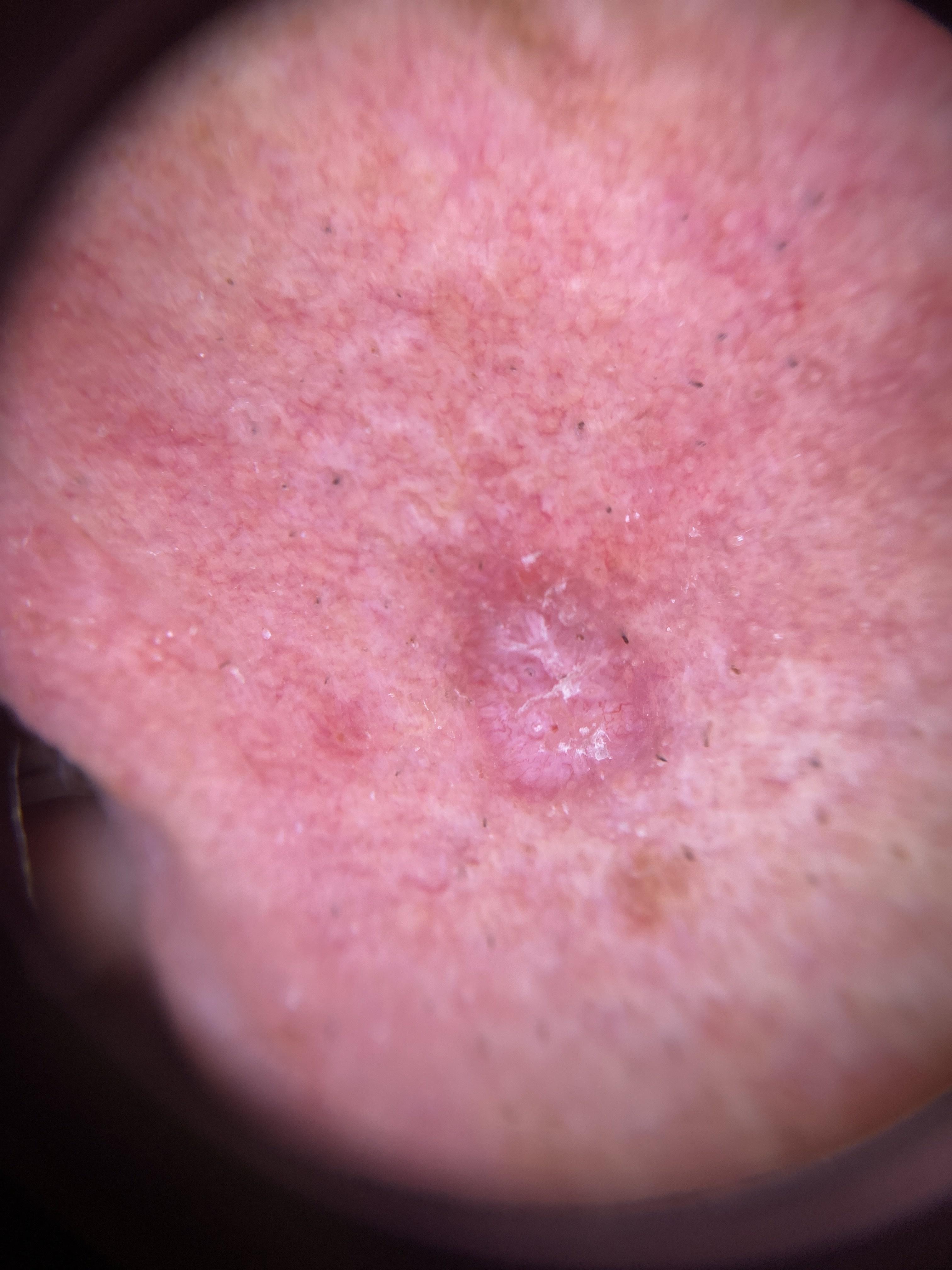The chart records a prior melanoma.
A dermoscopic close-up of a skin lesion.
A male patient approximately 80 years of age.
The lesion is on the head or neck.
On biopsy, the diagnosis was a malignant, epidermal lesion — a squamous cell carcinoma.